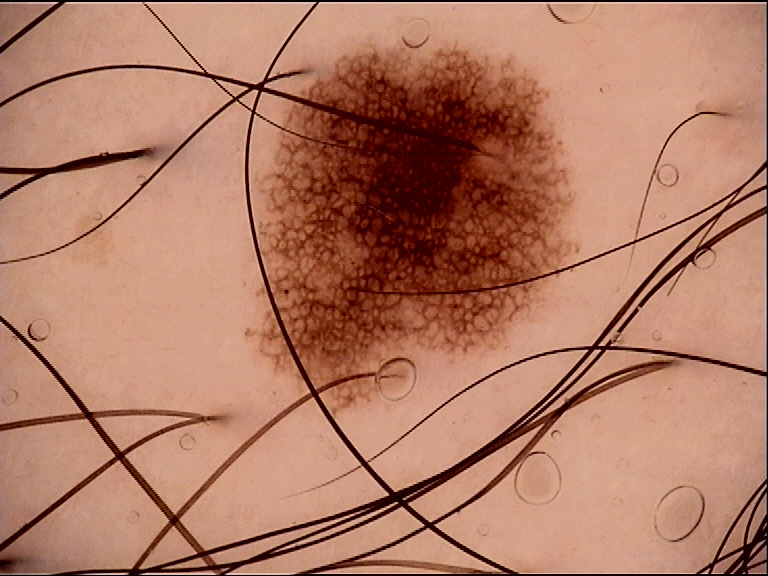Case: Dermoscopy of a skin lesion. Impression: The diagnostic label was a dysplastic junctional nevus.